The back of the torso is involved, the patient considered this a rash, close-up view, the lesion is associated with bothersome appearance — 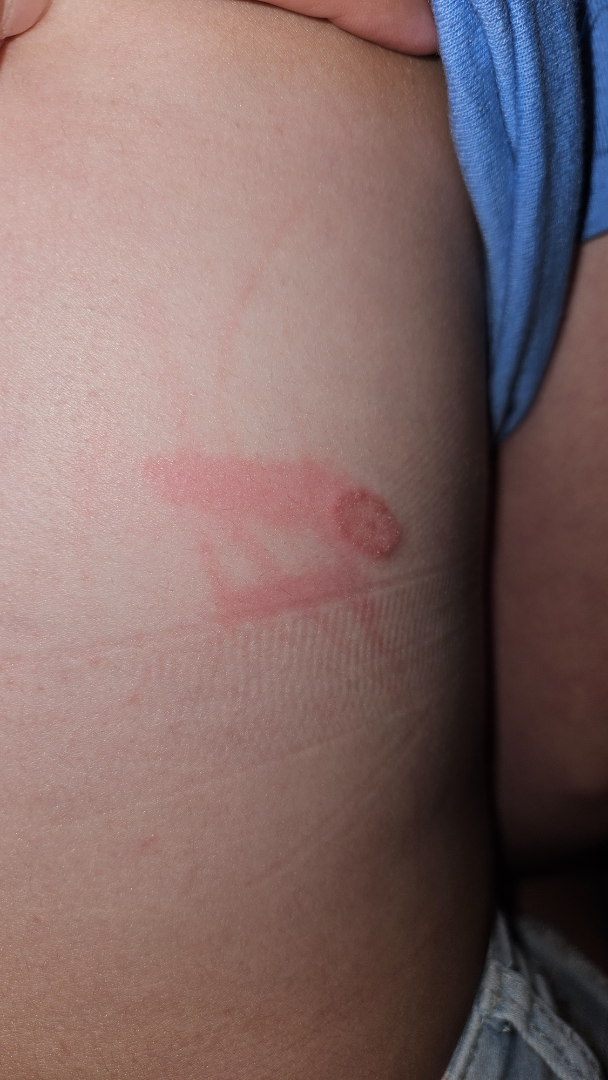diagnostic considerations: in keeping with Tinea.